An image taken at a distance. The subject is 18–29, female. The front of the torso is involved: 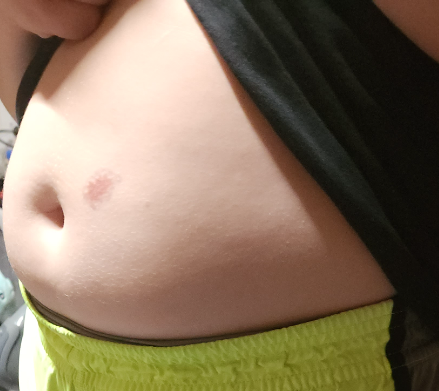| key | value |
|---|---|
| impression | most consistent with Melanocytic Nevus; also consider Atypical Nevus; possibly Melanoma |